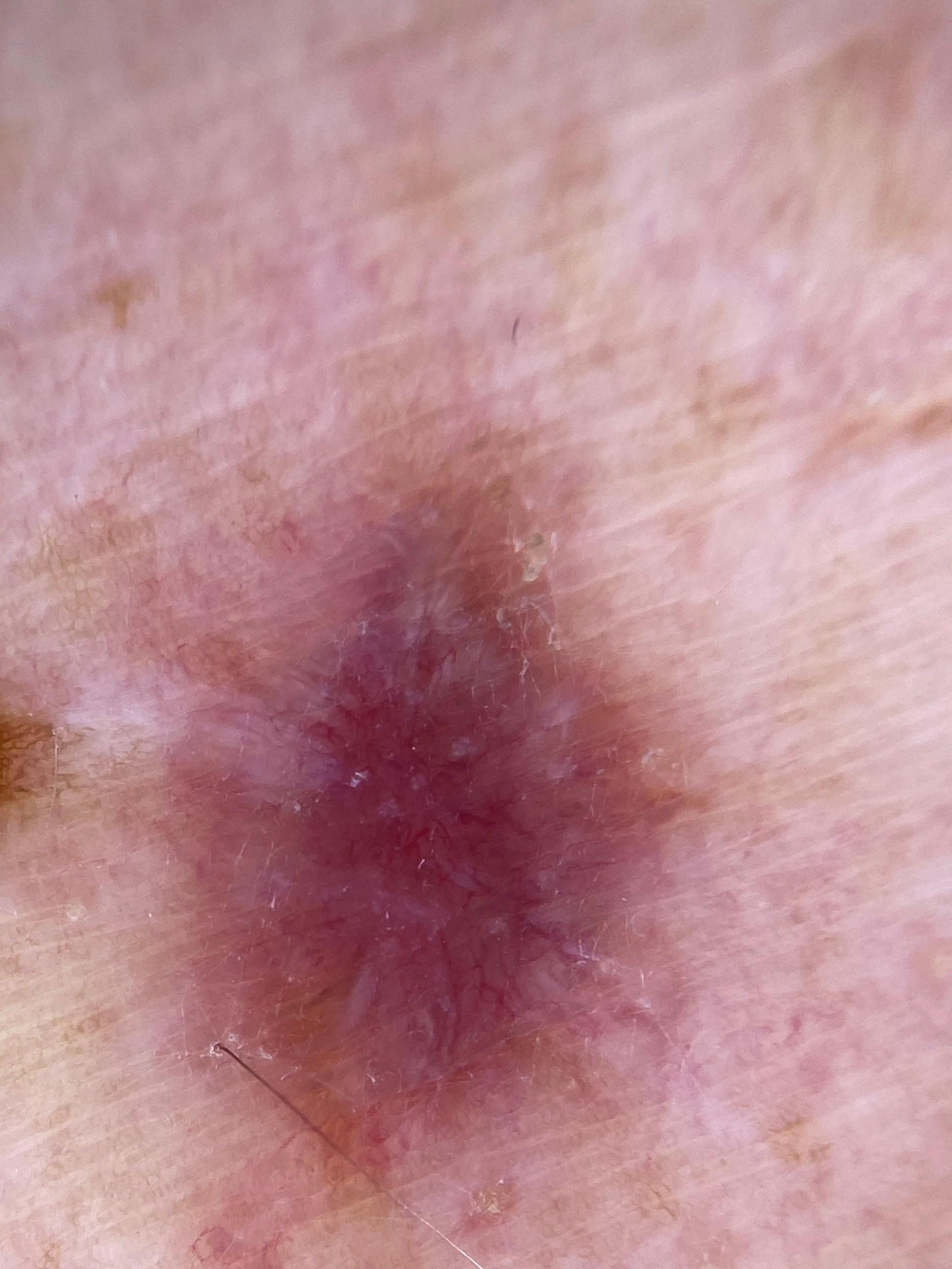<record>
  <diagnosis>
    <name>Basal cell carcinoma</name>
    <malignancy>malignant</malignancy>
    <confirmation>histopathology</confirmation>
    <lineage>adnexal</lineage>
  </diagnosis>
</record>